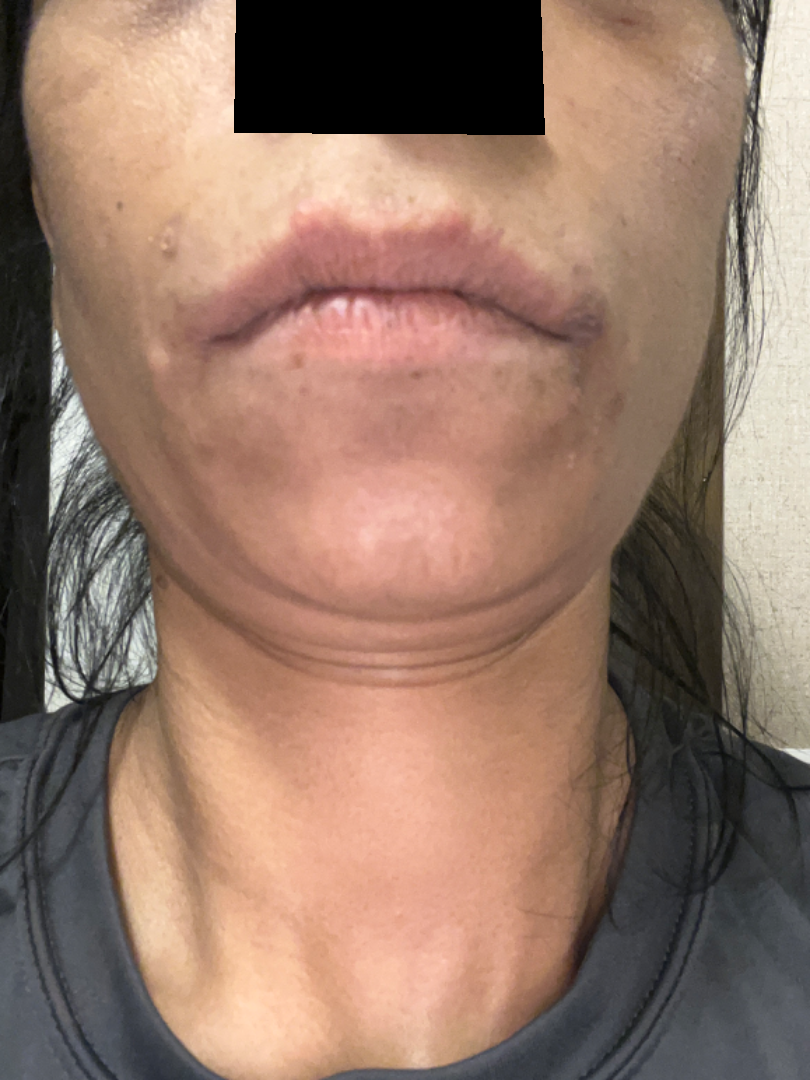anatomic site: head or neck and back of the torso
duration: one to three months
view: close-up
patient: female, age 30–39
patient-reported symptoms: bothersome appearance
impression: the leading consideration is Perioral Dermatitis; also consider Acne